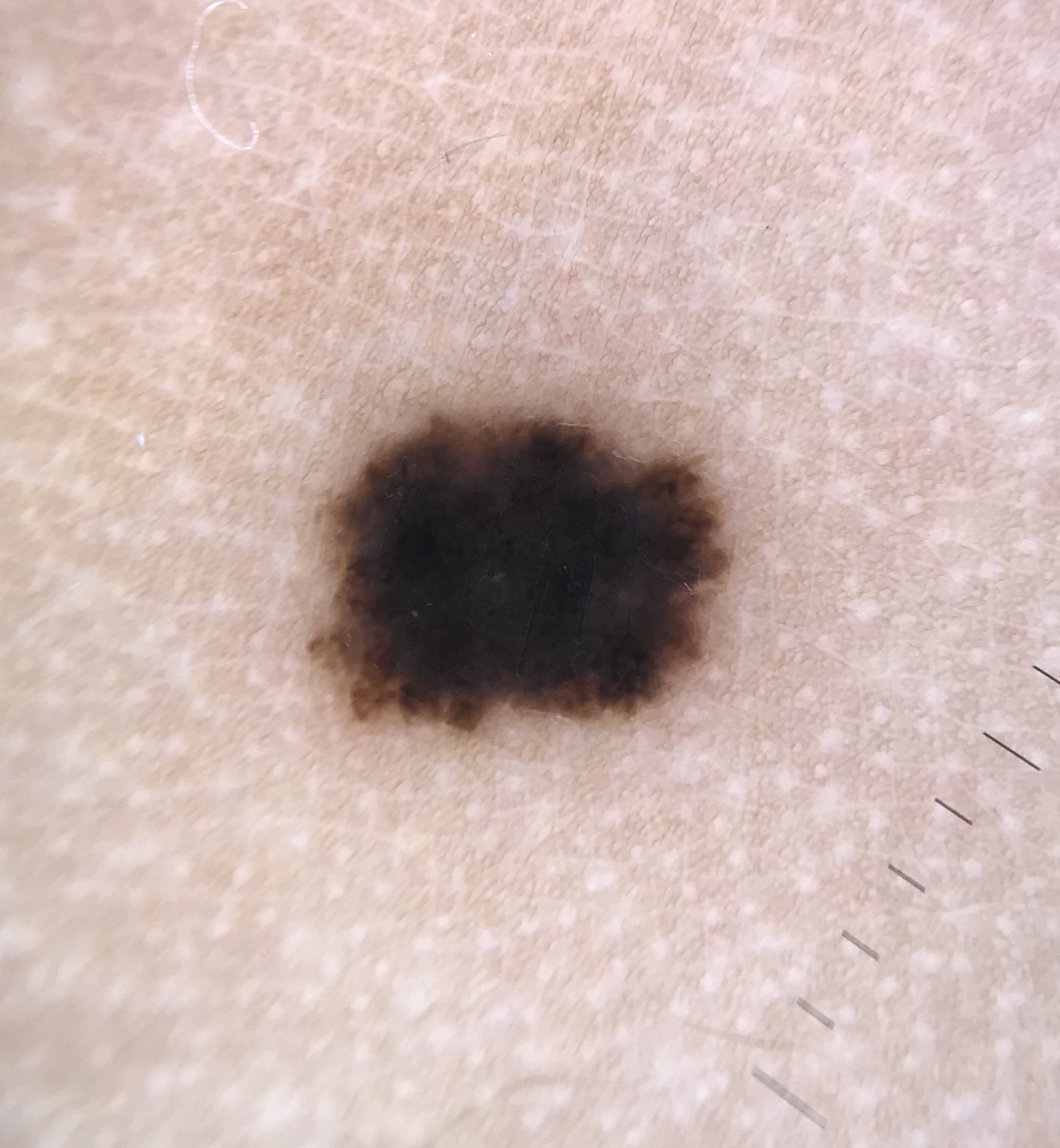Impression: Labeled as a Spitz/Reed nevus.